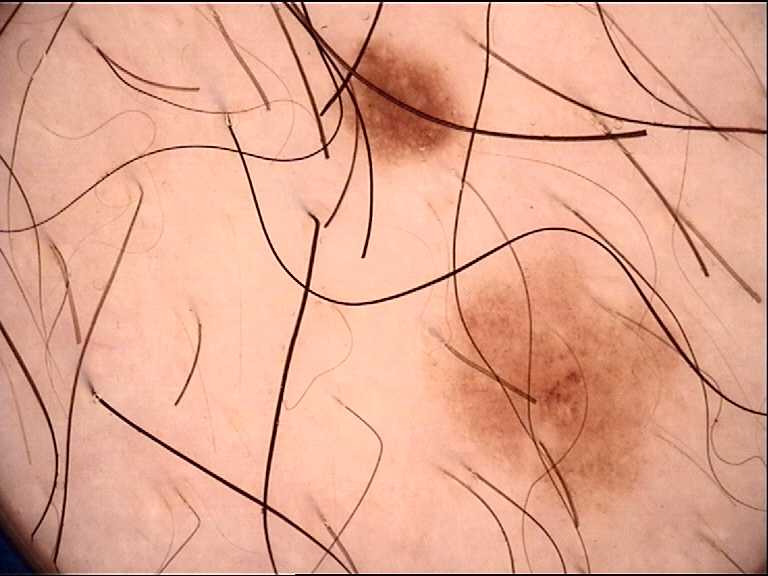<case>
  <diagnosis>
    <name>dysplastic junctional nevus</name>
    <code>jd</code>
    <malignancy>benign</malignancy>
    <super_class>melanocytic</super_class>
    <confirmation>expert consensus</confirmation>
  </diagnosis>
</case>